A dermoscopic close-up of a skin lesion.
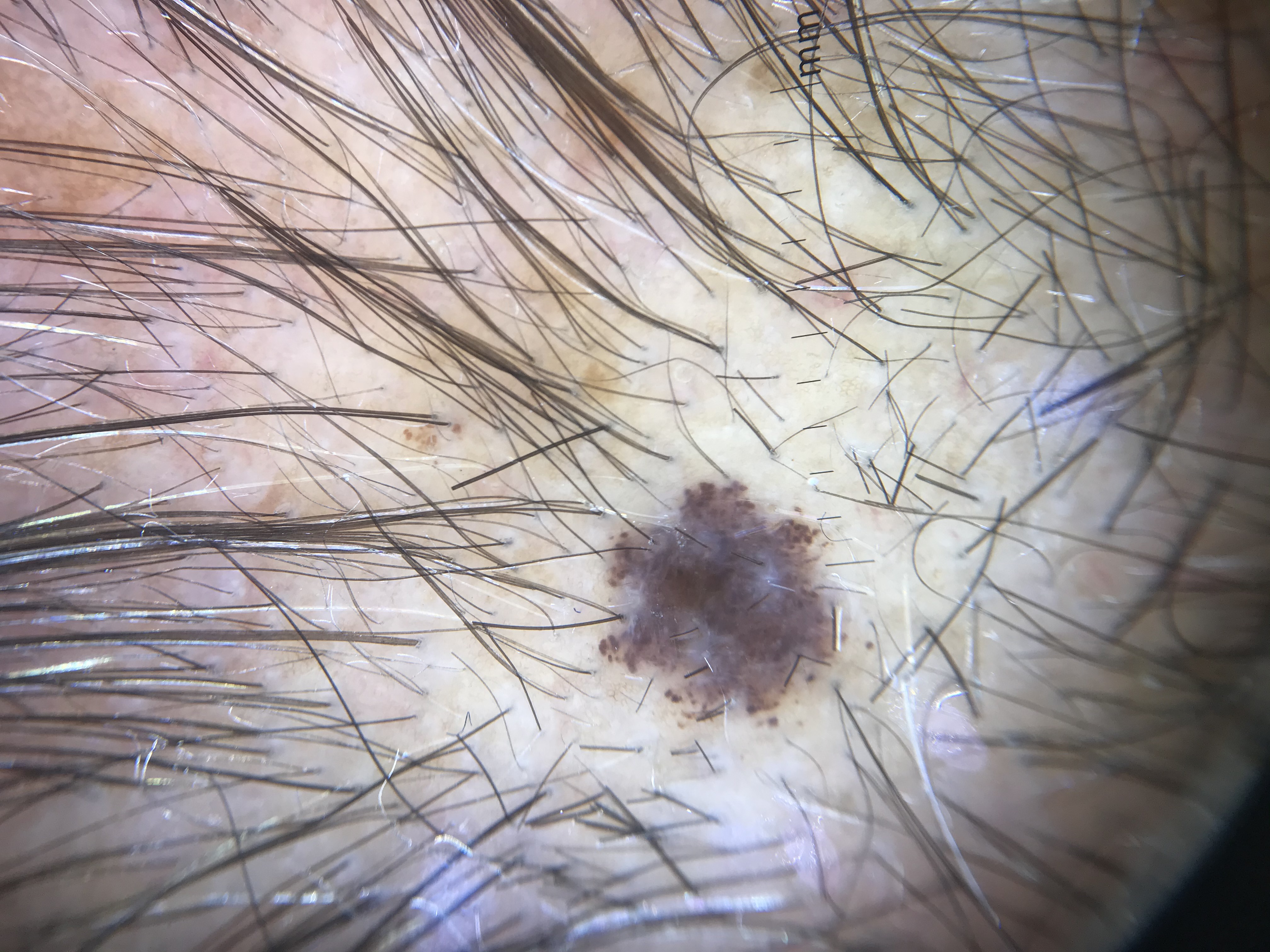Findings:
* class: dysplastic compound nevus (expert consensus)